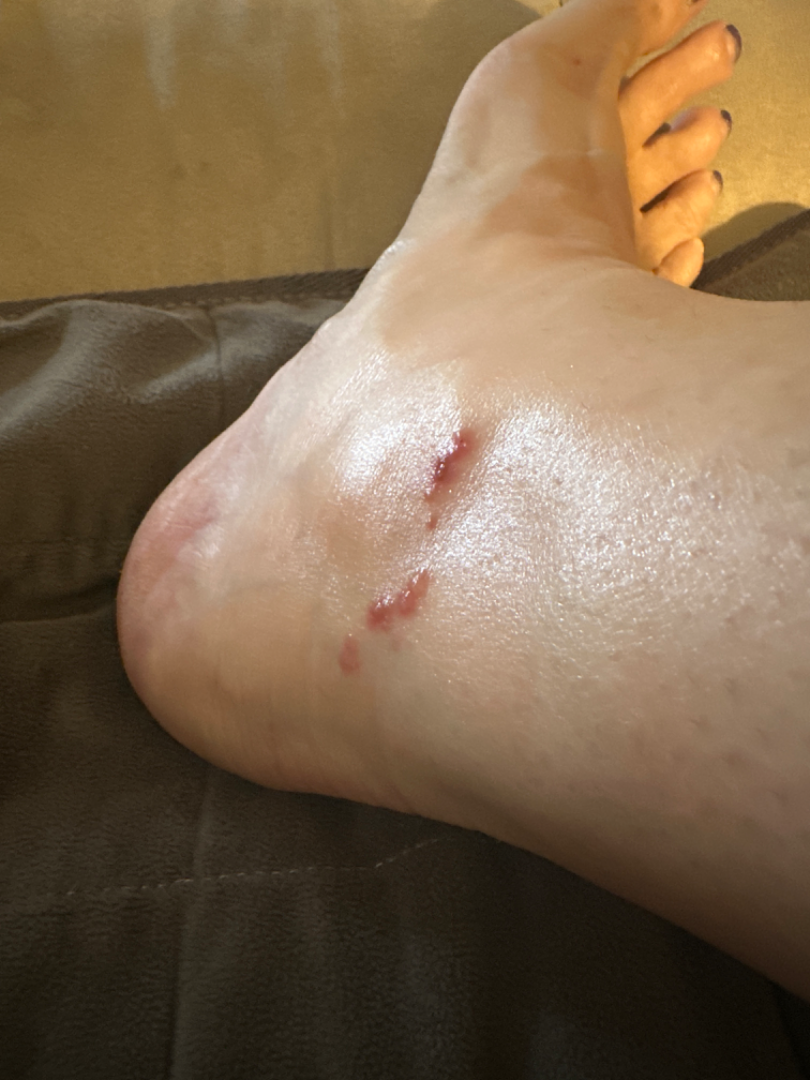{
  "assessment": "could not be assessed",
  "skin_tone": {
    "fitzpatrick": "IV",
    "monk_skin_tone": 3
  },
  "shot_type": "at an angle"
}